Self-categorized by the patient as a rash. Located on the top or side of the foot and sole of the foot. Reported duration is about one day. Female subject, age 40–49. Self-reported Fitzpatrick II. No associated lesion symptoms were reported. This is a close-up image. Texture is reported as raised or bumpy — 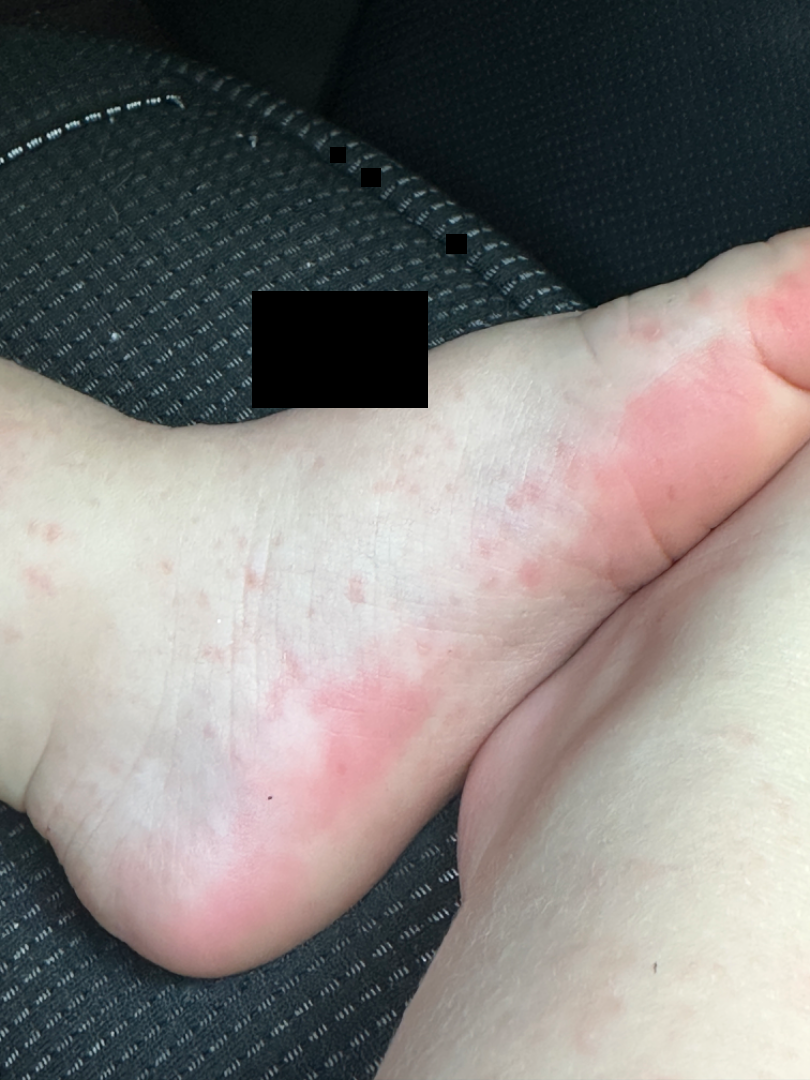assessment — unable to determine.